Located on the leg; an image taken at an angle — 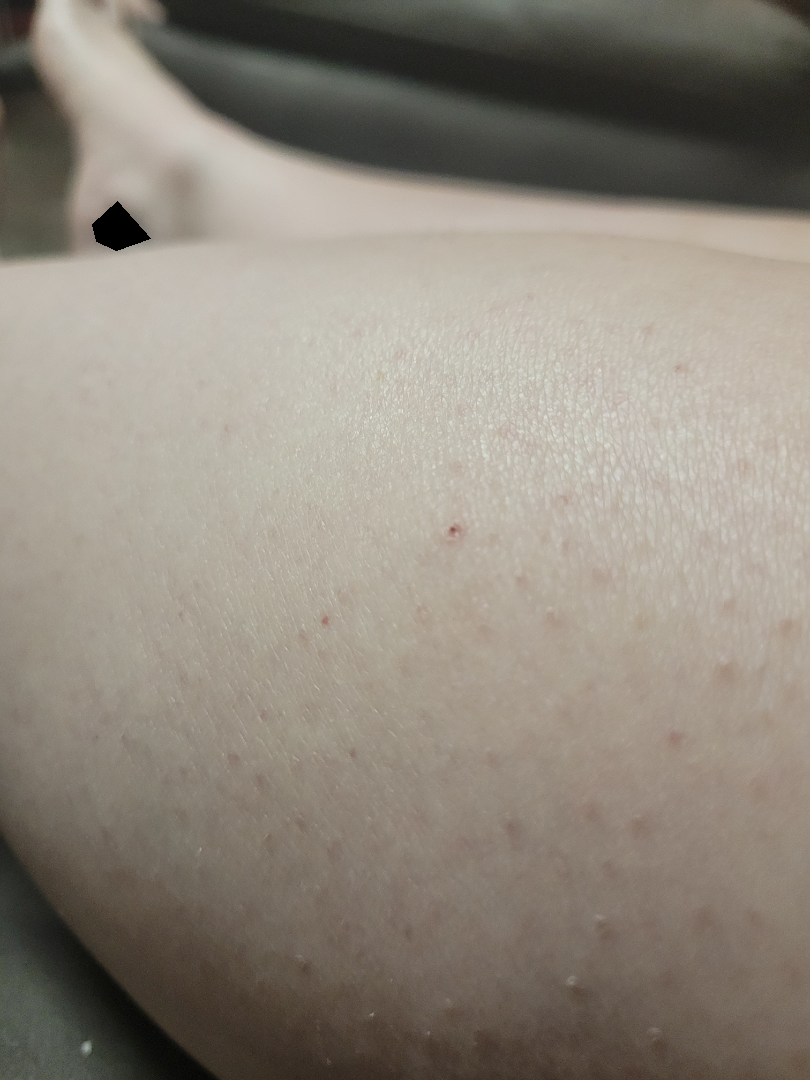The favored diagnosis is Keratosis pilaris; with consideration of Folliculitis.